A male subject, in their mid- to late 60s; a dermoscopic close-up of a skin lesion.
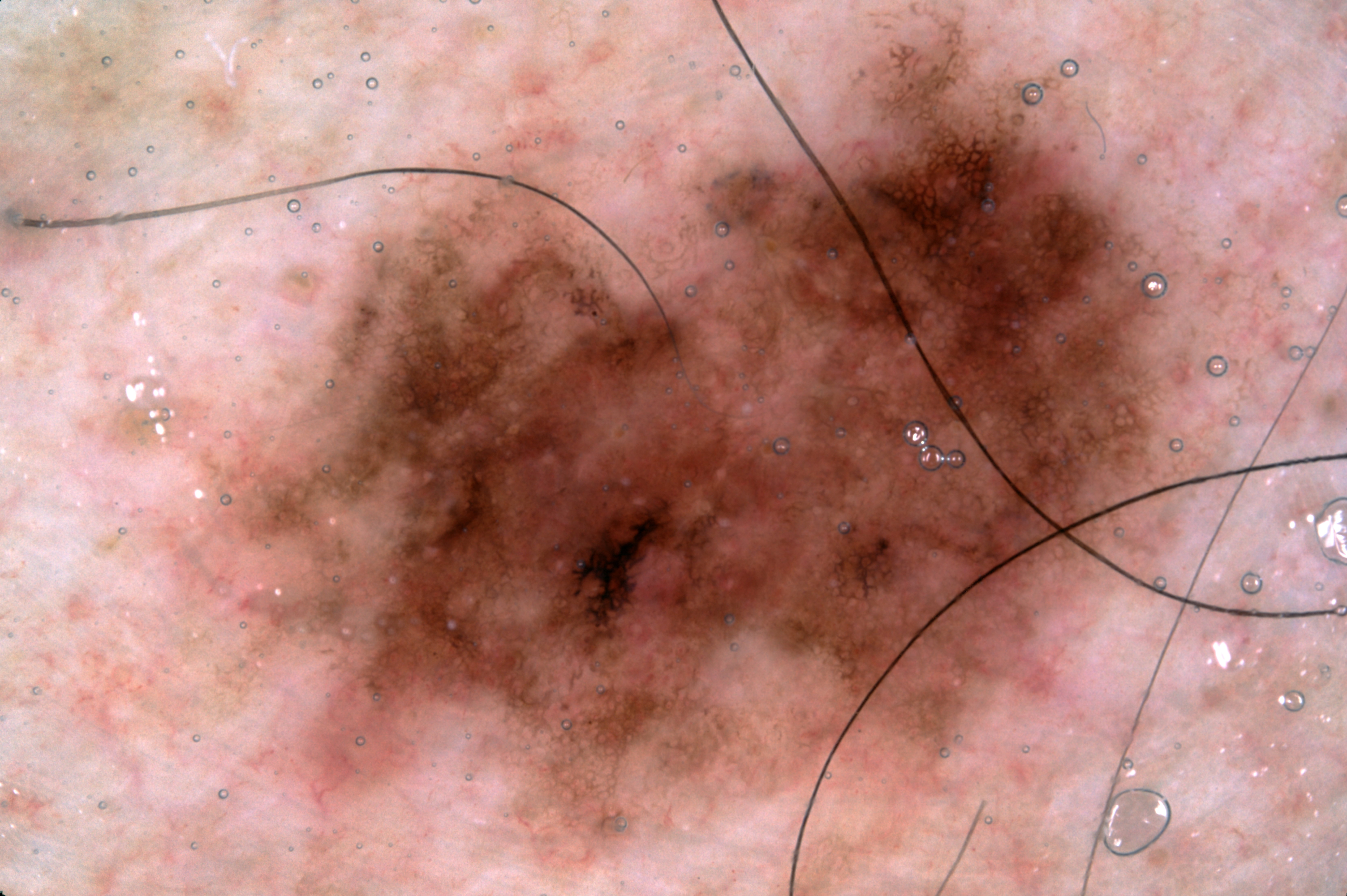lesion bbox = [179,42,1189,854]
dermoscopic findings = pigment network; absent: milia-like cysts, negative network, and streaks
impression = a melanocytic nevus, a benign skin lesion